A dermoscopy image of a single skin lesion; the subject is a female roughly 35 years of age: 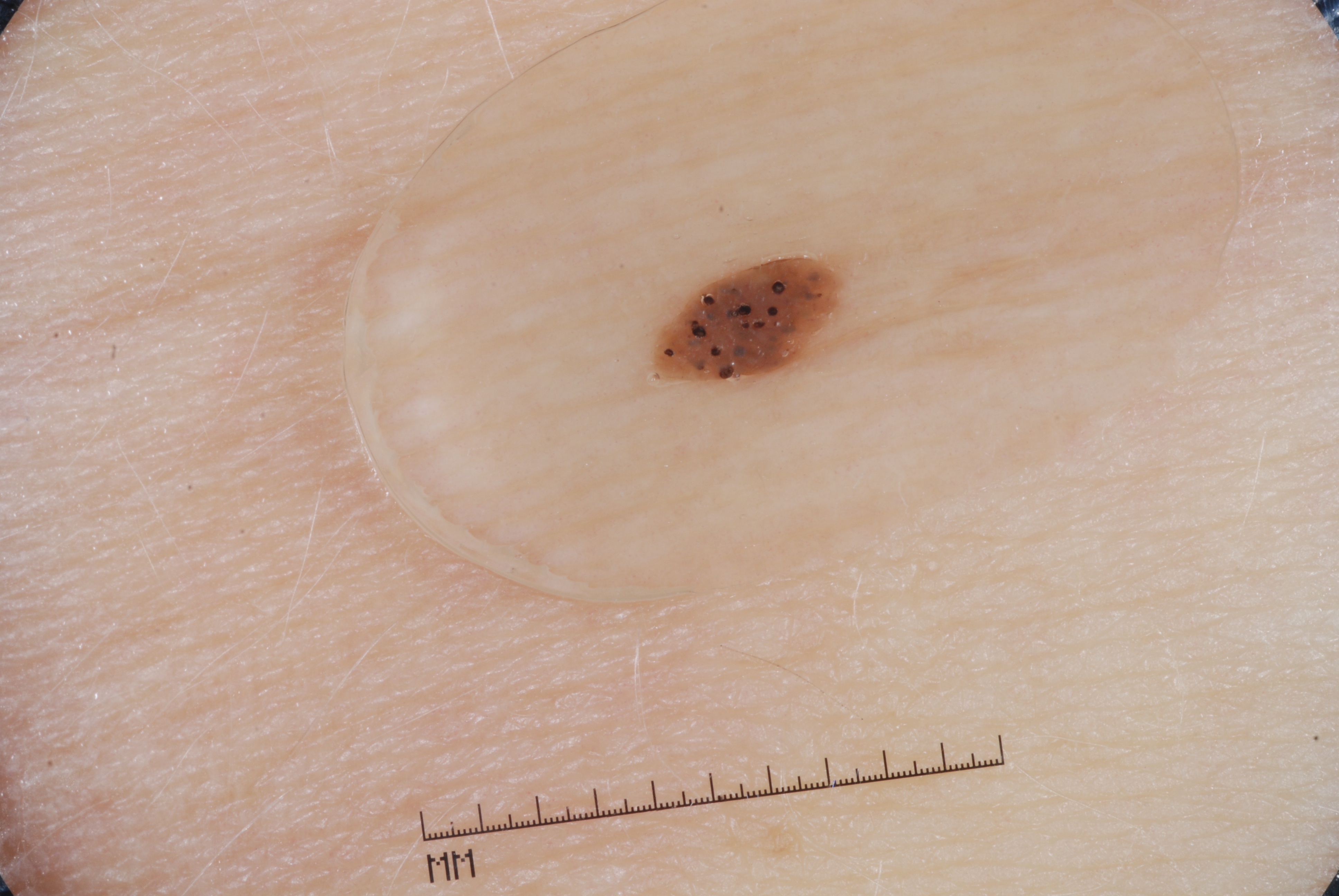bounding box = 653/255/844/385 | dermoscopic findings = milia-like cysts; absent: negative network, streaks, and pigment network | lesion size = ~1% of the field | assessment = a seborrheic keratosis, a benign skin lesion.